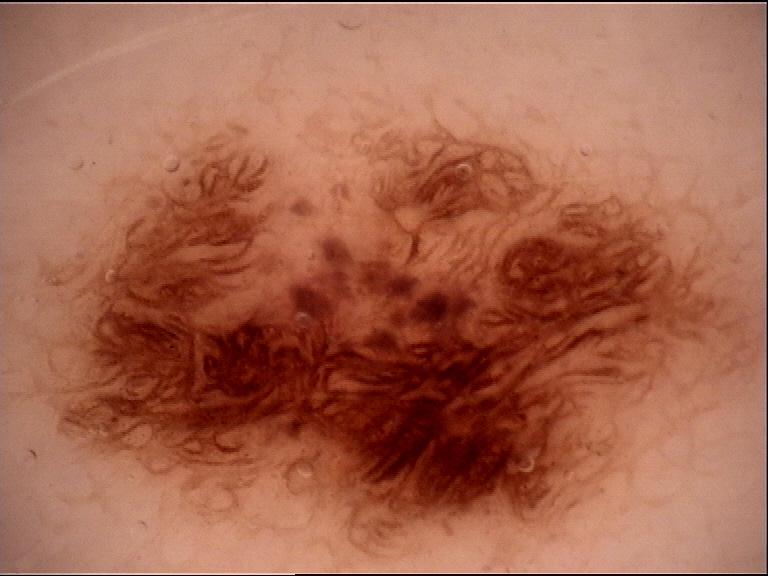diagnostic label — dysplastic junctional nevus (expert consensus).